The patient is a female in their mid-50s; dermoscopy of a skin lesion — 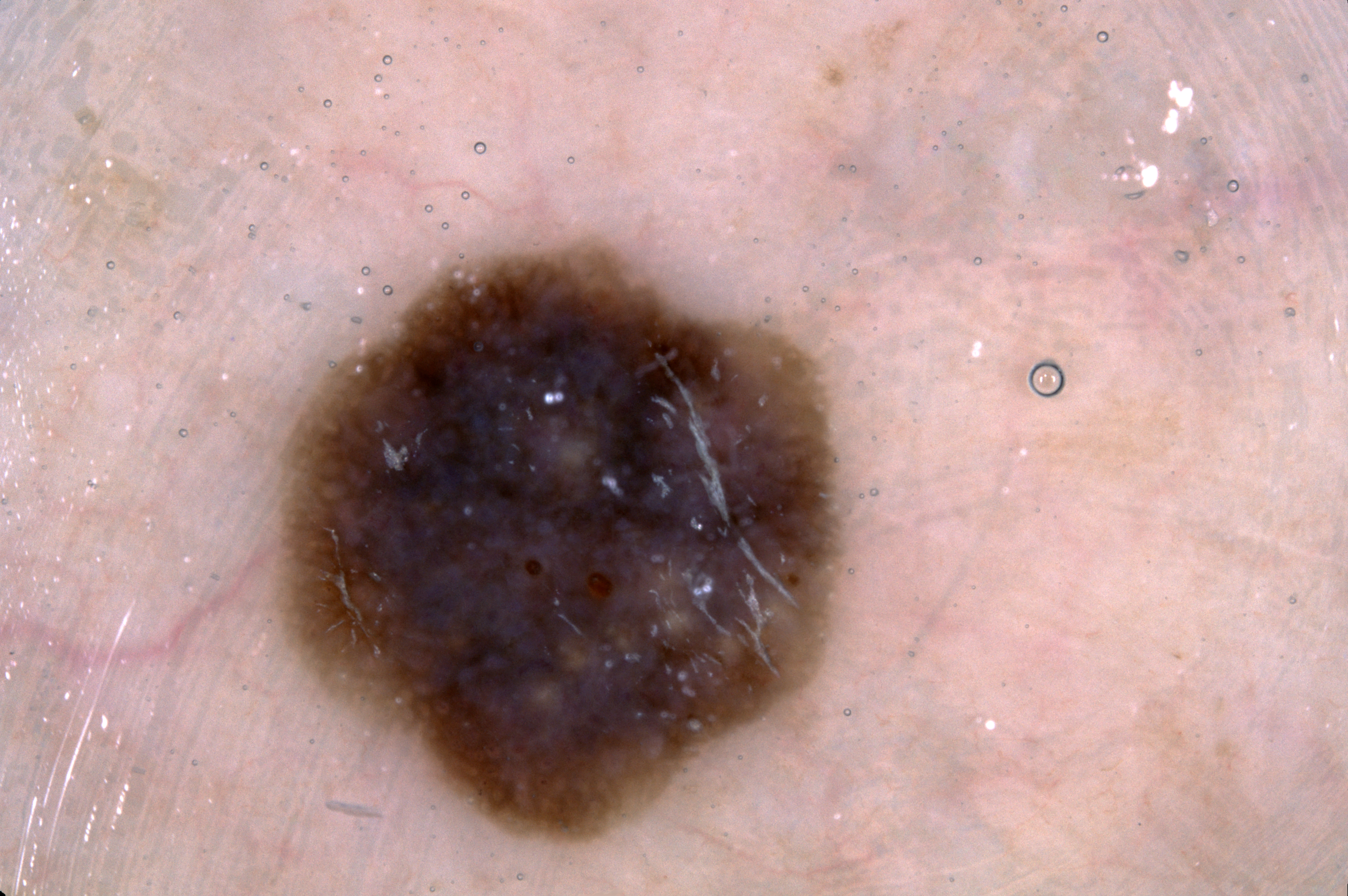Findings:
- lesion extent — moderate
- dermoscopic findings — pigment network and milia-like cysts; absent: negative network and streaks
- location — (285, 245, 842, 847)
- diagnosis — a seborrheic keratosis